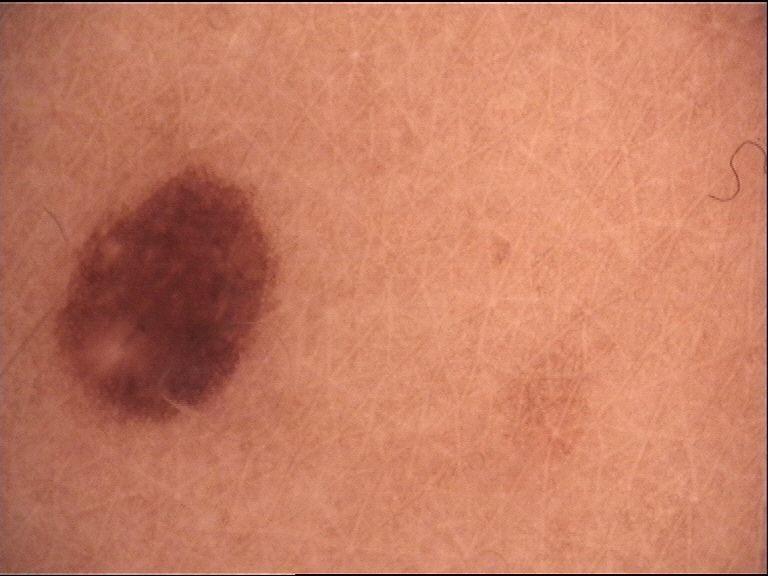– image: dermoscopy
– class: junctional nevus (expert consensus)